Female subject, age 40–49. The affected area is the arm. An image taken at a distance: 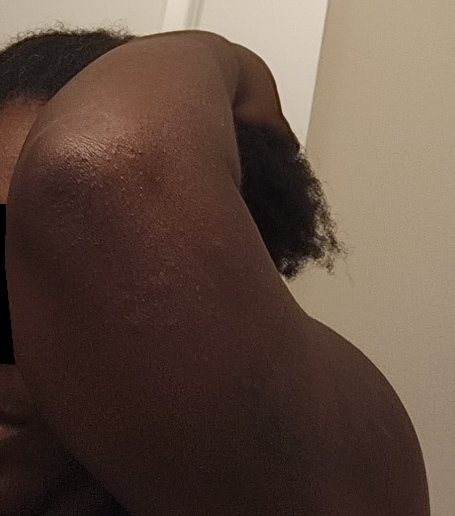Findings:
– differential diagnosis — the impression on review was Keratosis pilaris